A dermoscopy image of a single skin lesion:
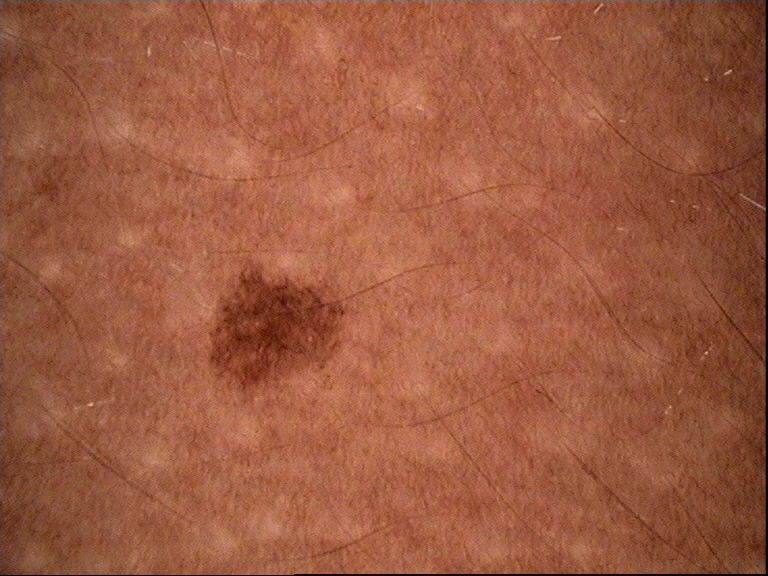Summary: The architecture is that of a banal lesion. Conclusion: Classified as a junctional nevus.